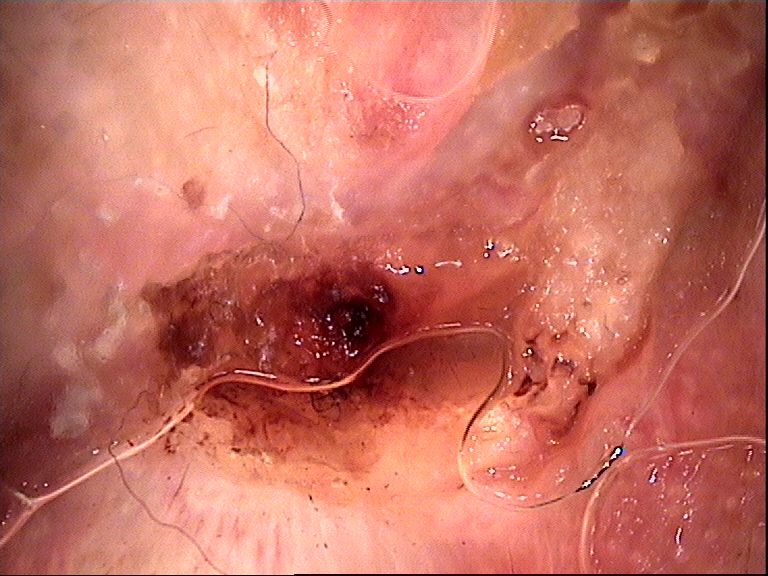image type — dermoscopy
category — keratinocytic
diagnostic label — squamous cell carcinoma (biopsy-proven)